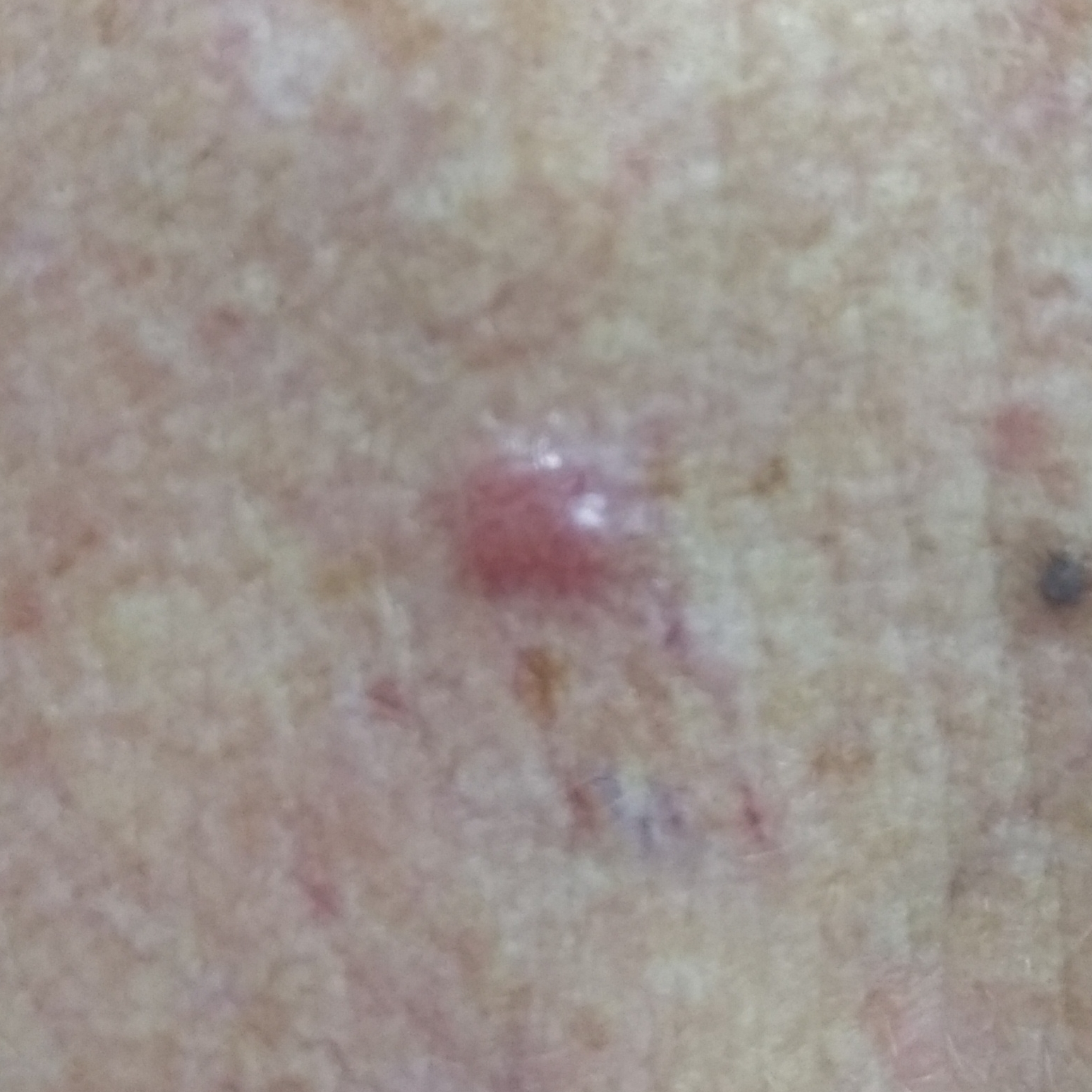Histopathological examination showed a basal cell carcinoma.